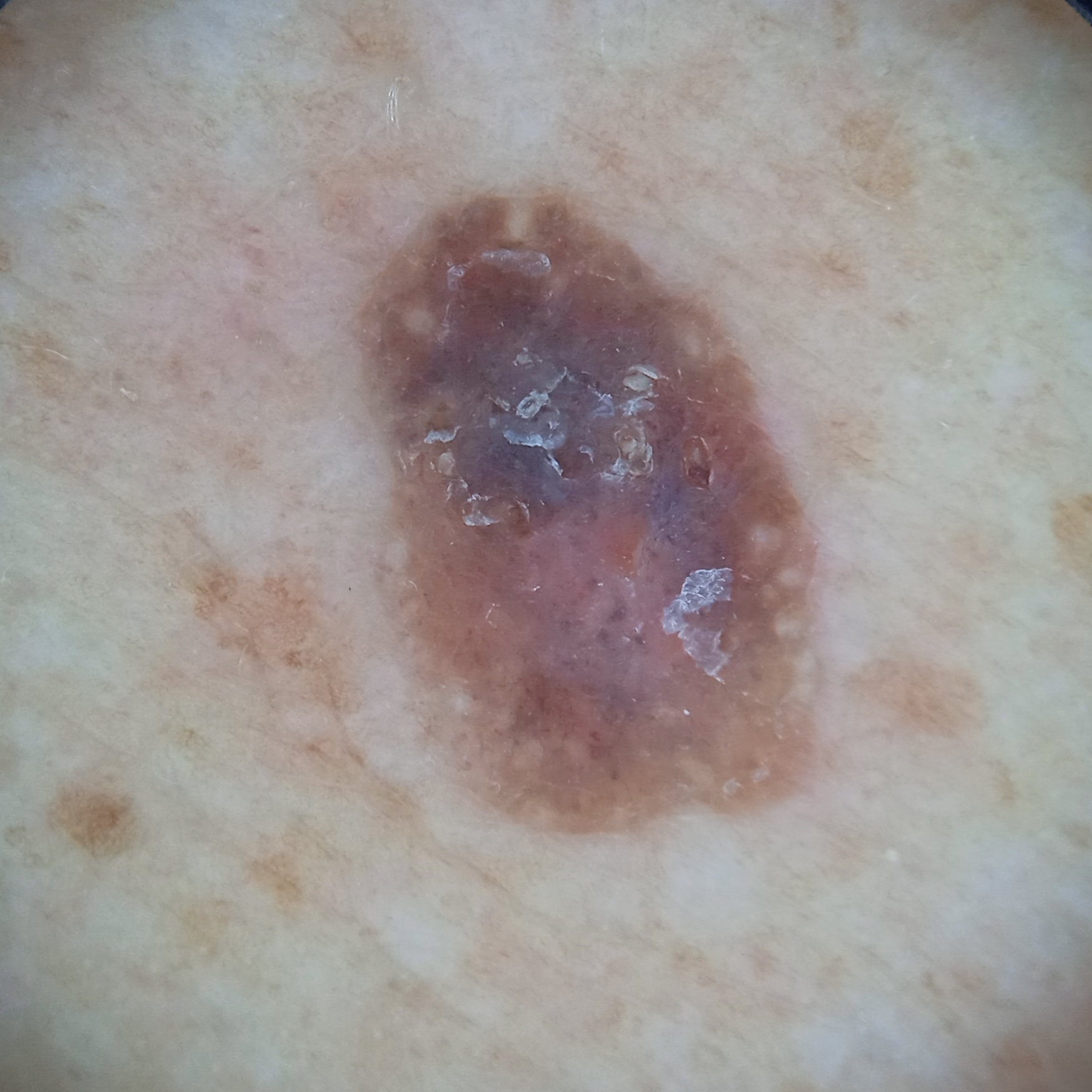diagnostic label=seborrheic keratosis (dermatologist consensus)